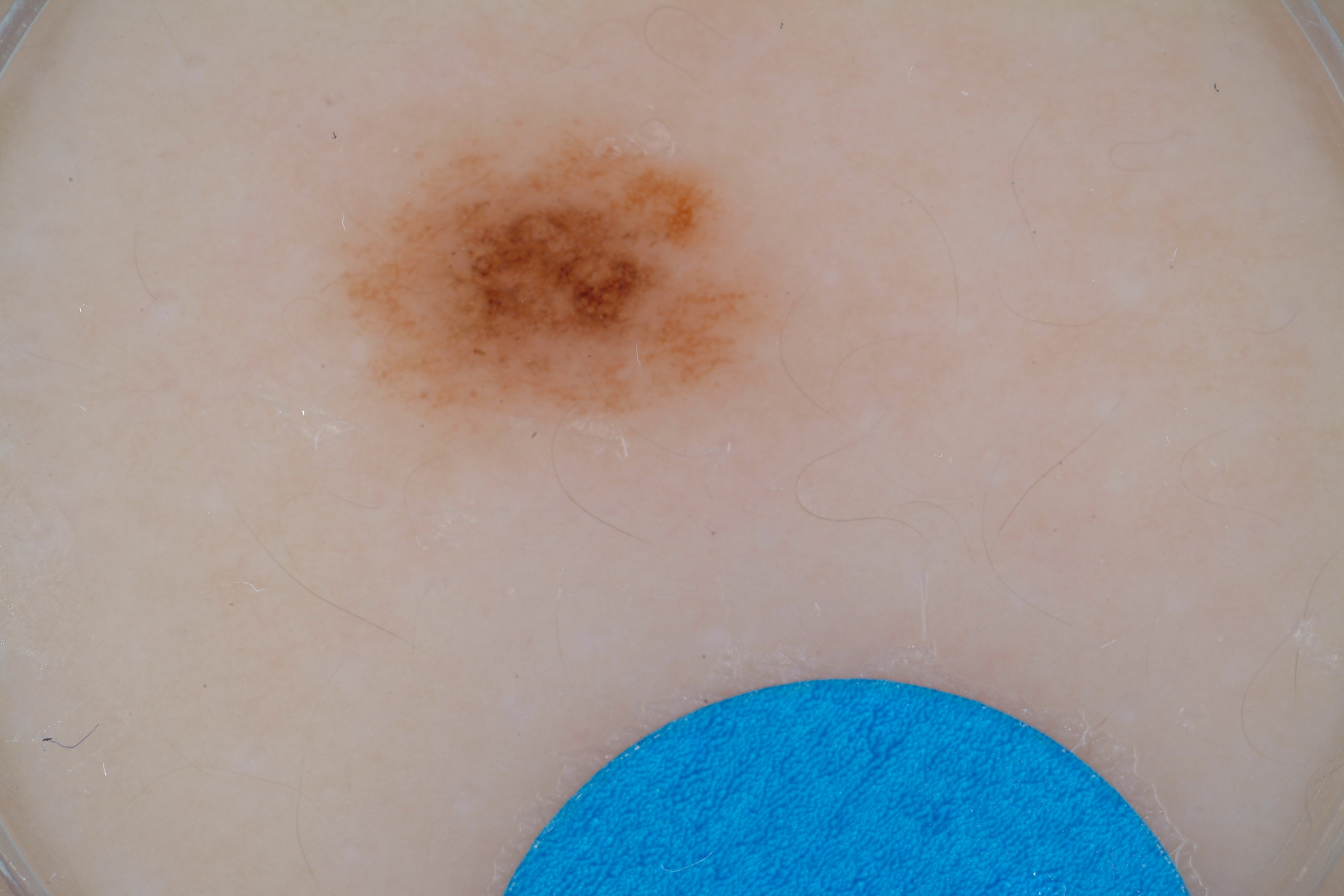- subject — female, aged around 10
- image type — dermoscopy
- dermoscopic pattern — pigment network; absent: streaks, globules, milia-like cysts, and negative network
- location — 338, 115, 782, 435
- lesion size — moderate
- assessment — a melanocytic nevus, a benign lesion